Located on the leg; this is a close-up image — 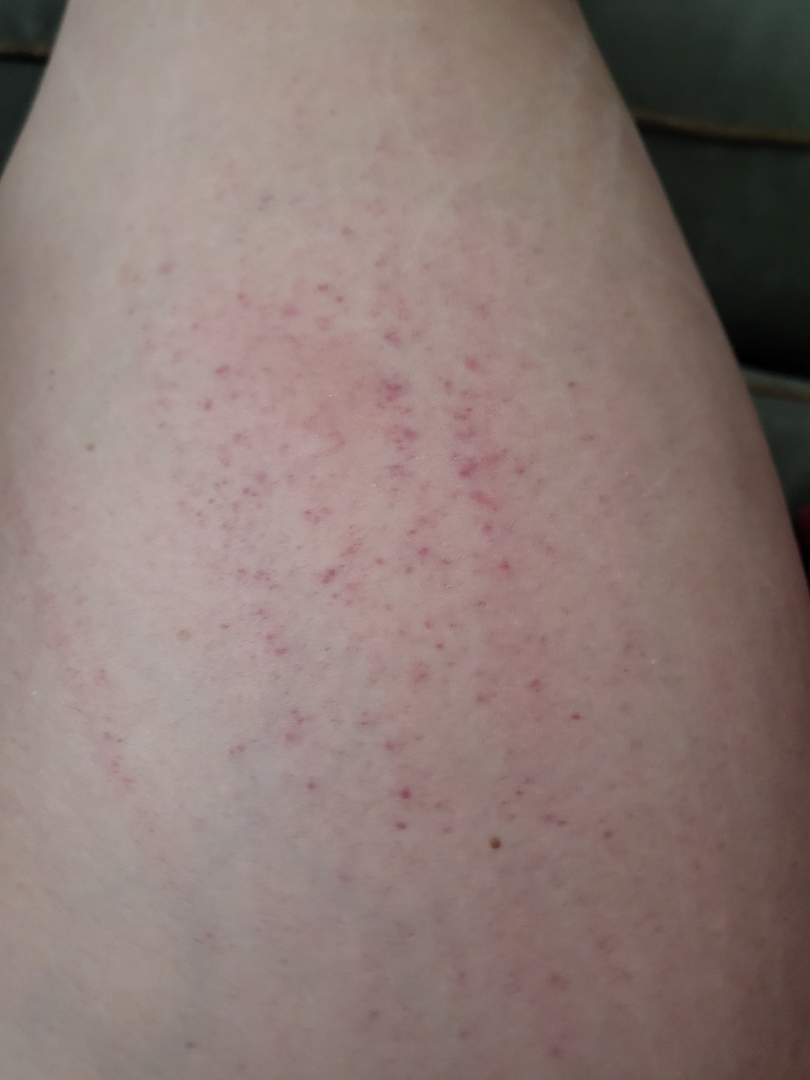Assessment:
The reviewing dermatologists' impression was: the leading consideration is Traumatic petechiae; lower on the differential is Acute dermatitis, NOS; less likely is Irritant Contact Dermatitis; less probable is Abrasion, scrape, or scab; a more distant consideration is Petechiae; a remote consideration is Pigmented purpuric eruption.